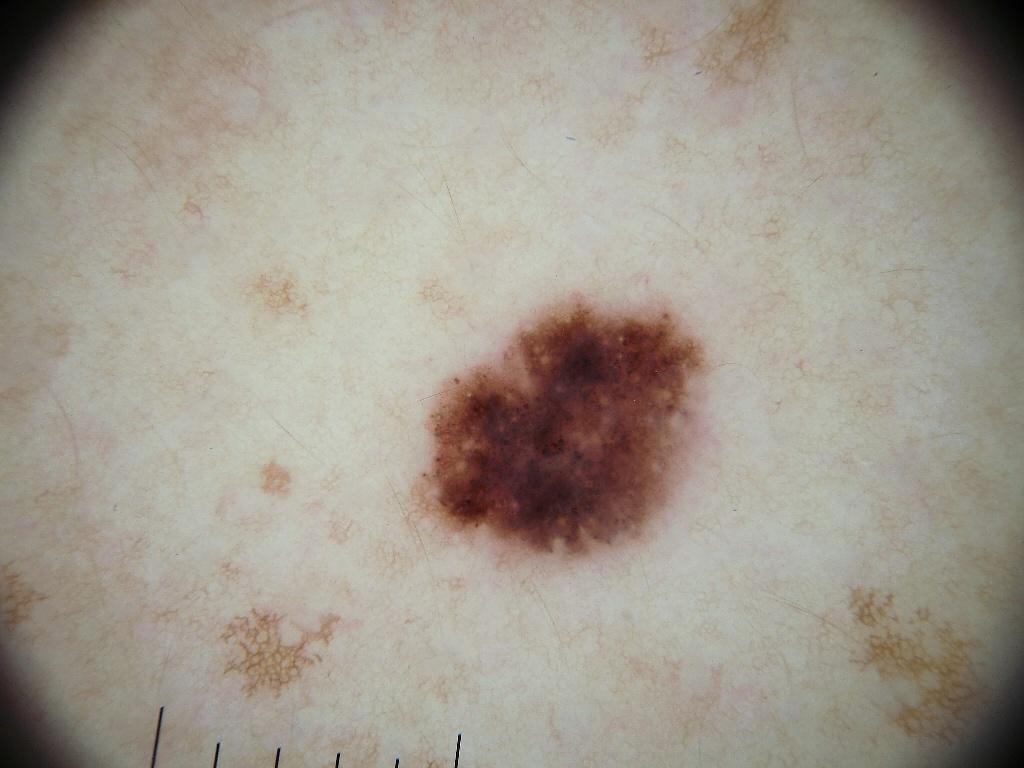<case>
<image>
  <modality>dermoscopy</modality>
</image>
<lesion_location>
  <bbox_xyxy>413, 294, 708, 565</bbox_xyxy>
</lesion_location>
<diagnosis>
  <name>melanocytic nevus</name>
  <malignancy>benign</malignancy>
  <lineage>melanocytic</lineage>
  <provenance>clinical</provenance>
</diagnosis>
</case>